A dermoscopy image of a single skin lesion.
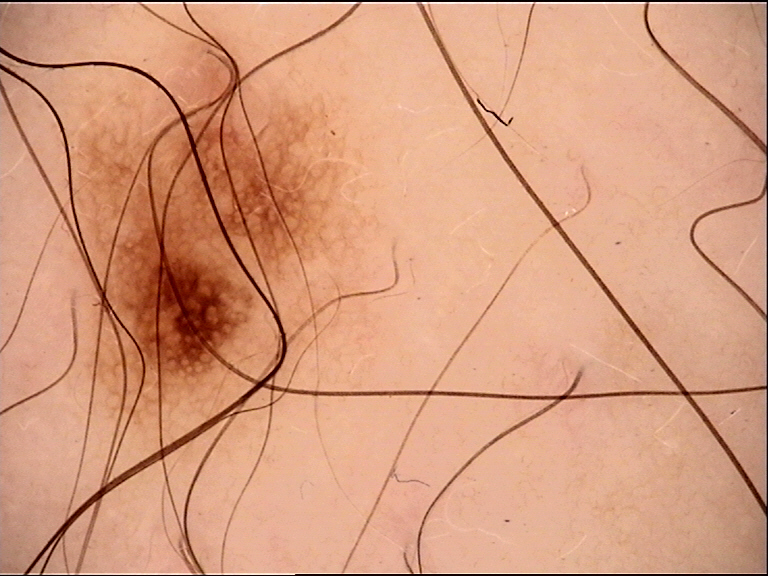Impression: The diagnosis was a dysplastic junctional nevus.